A clinical photo of a skin lesion taken with a smartphone · a patient 64 years of age.
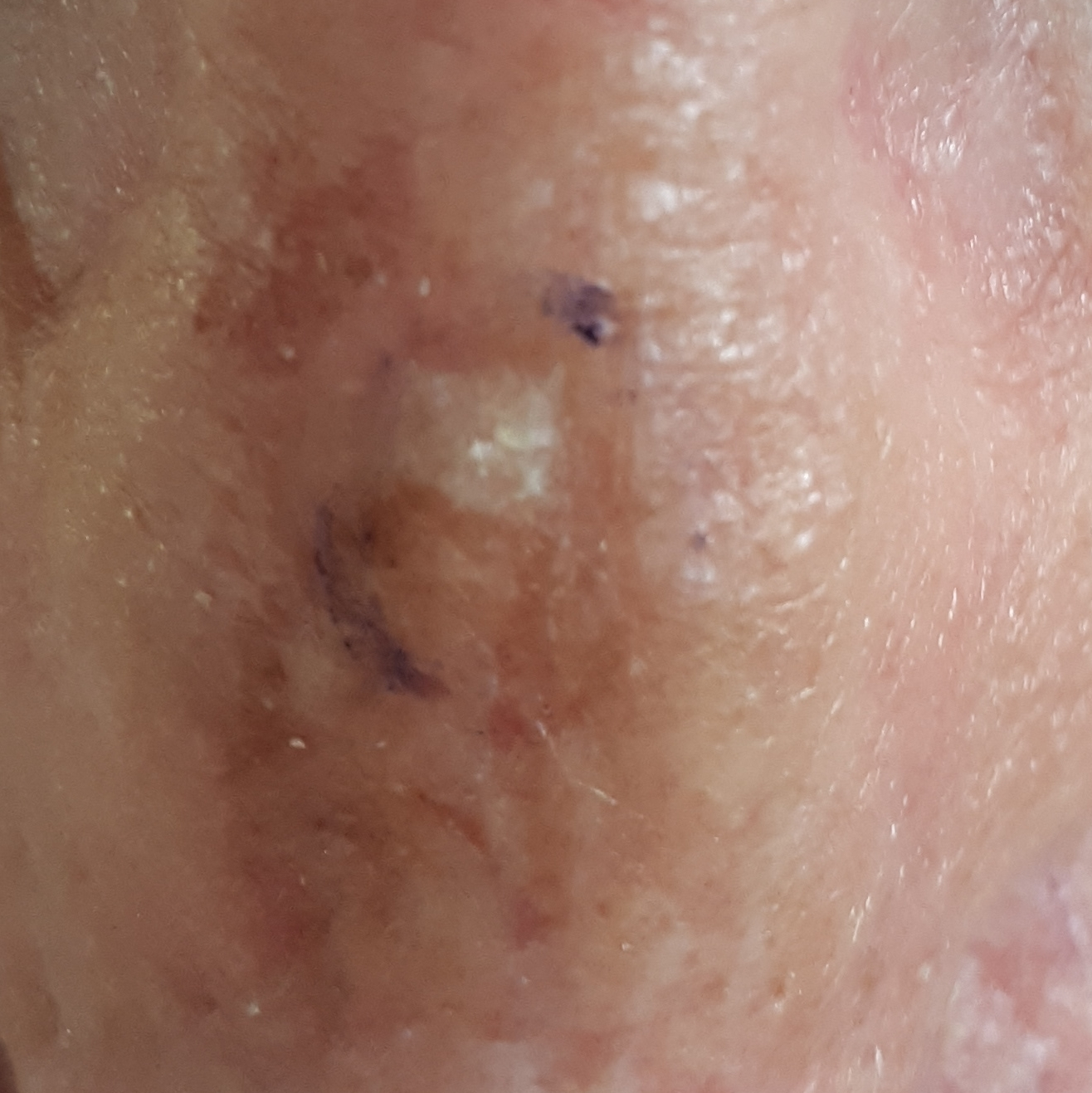  diagnosis:
    name: actinic keratosis
    code: ACK
    malignancy: indeterminate
    confirmation: clinical consensus